The patient notes the condition has been present for about one day, the contributor is a female aged 18–29, the leg is involved, the patient notes the lesion is raised or bumpy, a close-up photograph, the patient notes itching and enlargement, the patient described the issue as a rash:
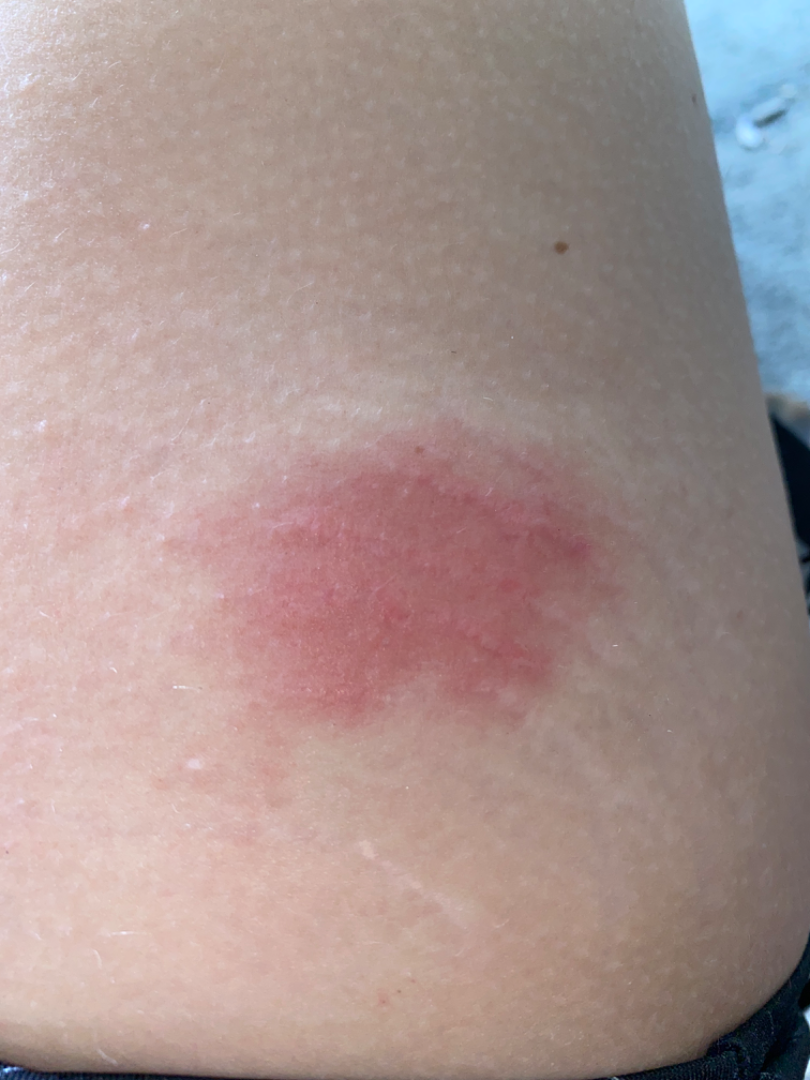{"differential": {"leading": ["Acute dermatitis, NOS"]}}